A dermoscopic image of a skin lesion.
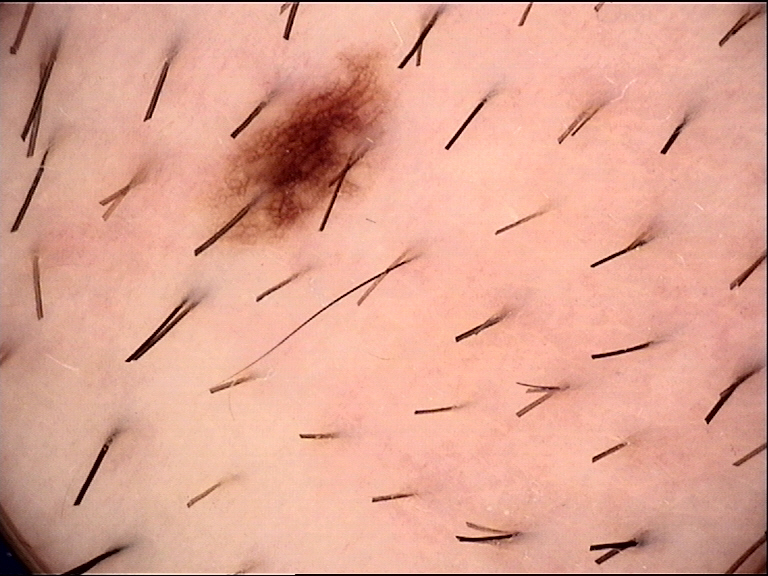Classified as a benign lesion — a dysplastic junctional nevus.